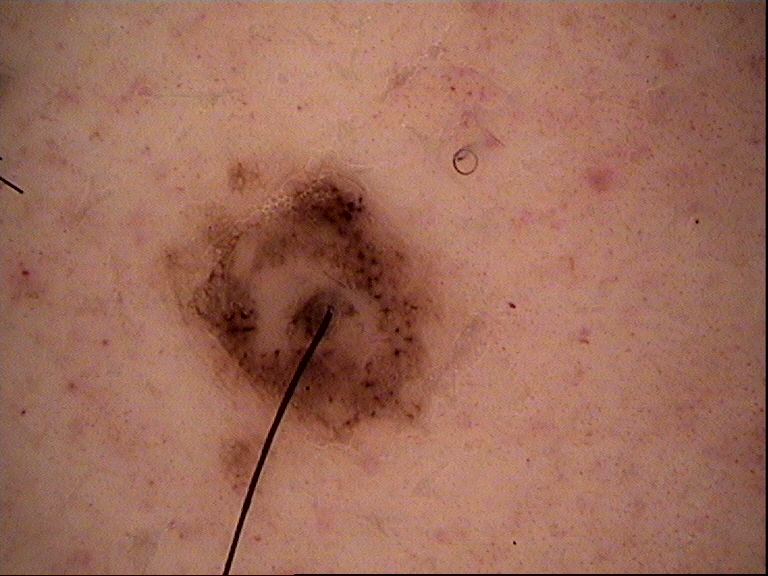Consistent with a banal lesion — a compound nevus.